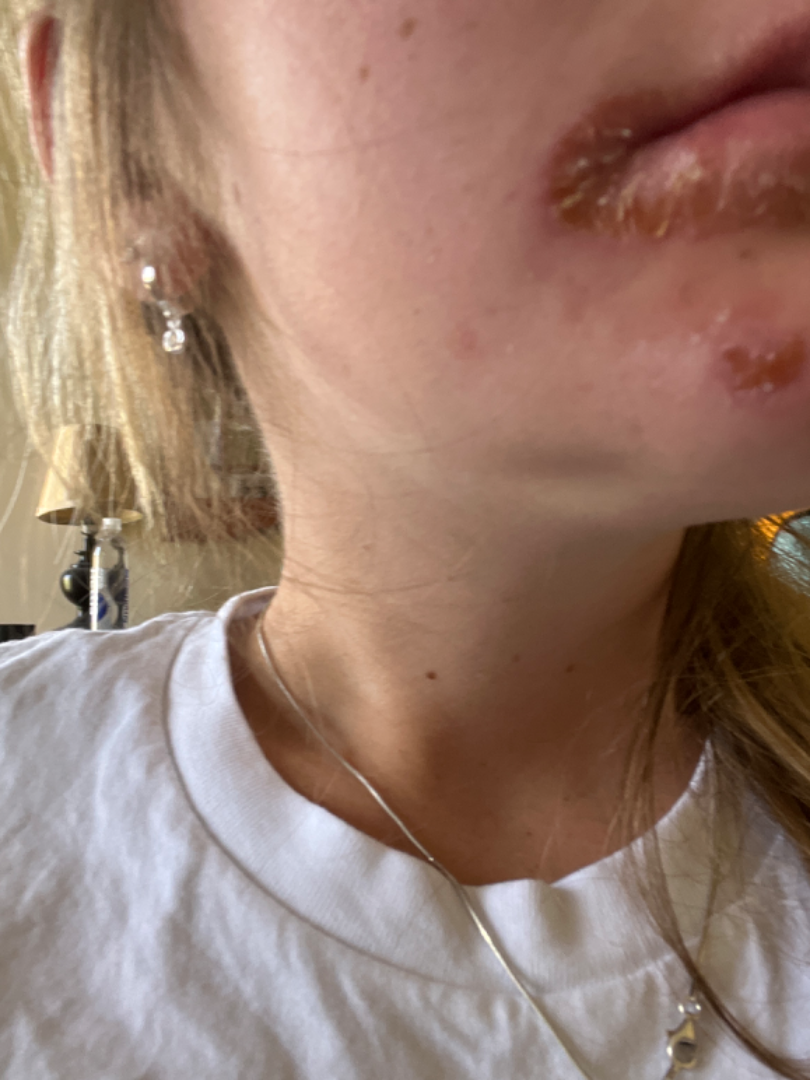The head or neck is involved. Texture is reported as rough or flaky. The contributor notes darkening, bothersome appearance and enlargement. Associated systemic symptoms include mouth sores. The photograph was taken at a distance. The contributor notes the condition has been present for less than one week. In keeping with Impetigo.